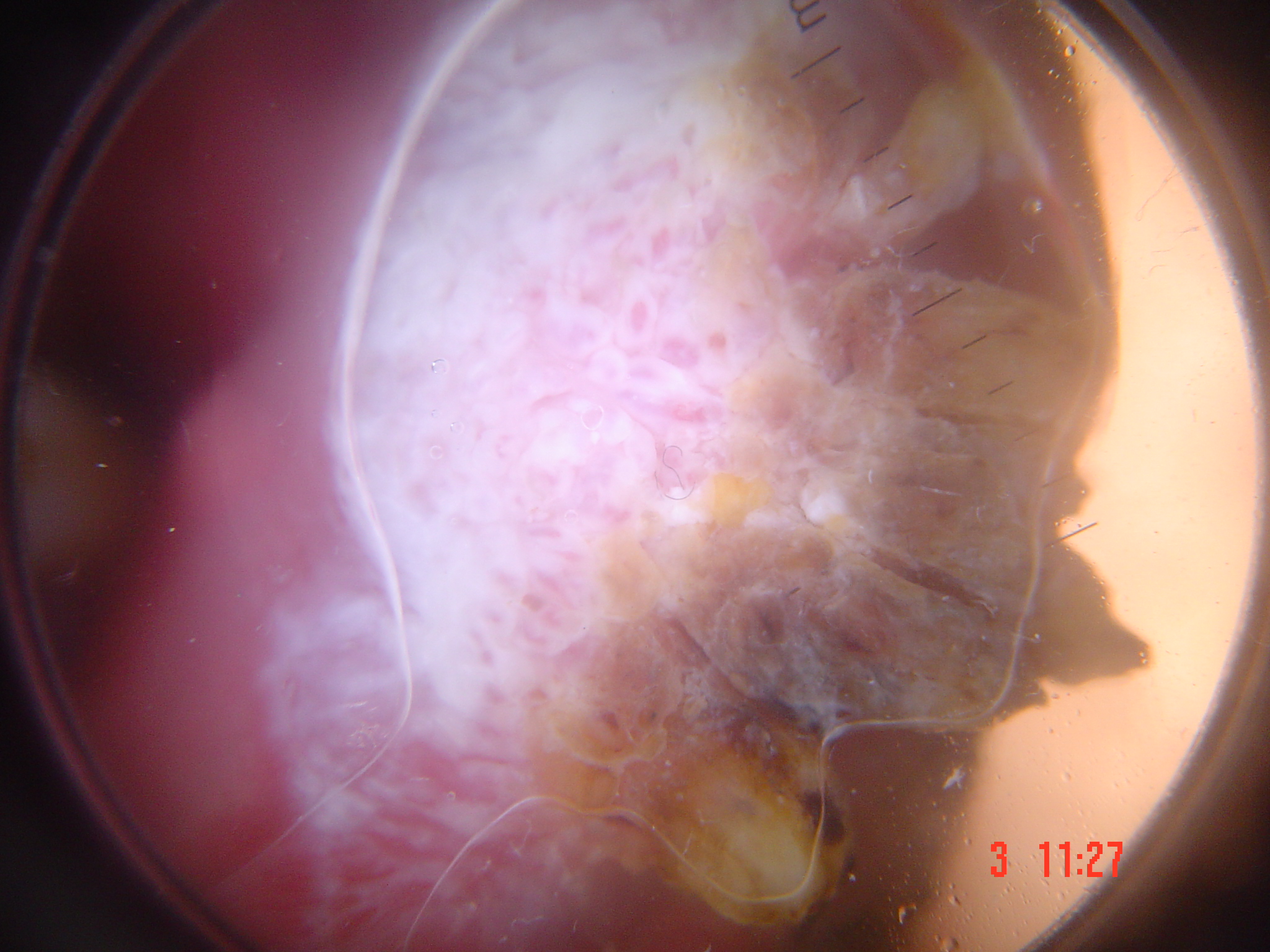• image type · dermatoscopy
• category · keratinocytic
• diagnostic label · squamous cell carcinoma (biopsy-proven)